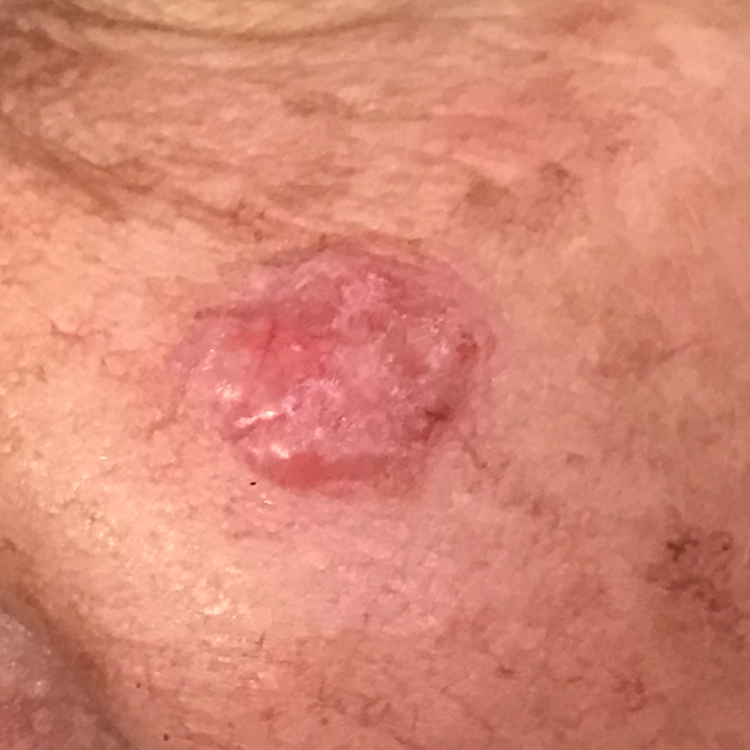The patient is FST II.
A clinical close-up photograph of a skin lesion.
The lesion involves the face.
The lesion is roughly 12 by 11 mm.
By the patient's account, the lesion itches, is elevated, and has grown.
The biopsy diagnosis was a malignancy — a basal cell carcinoma.